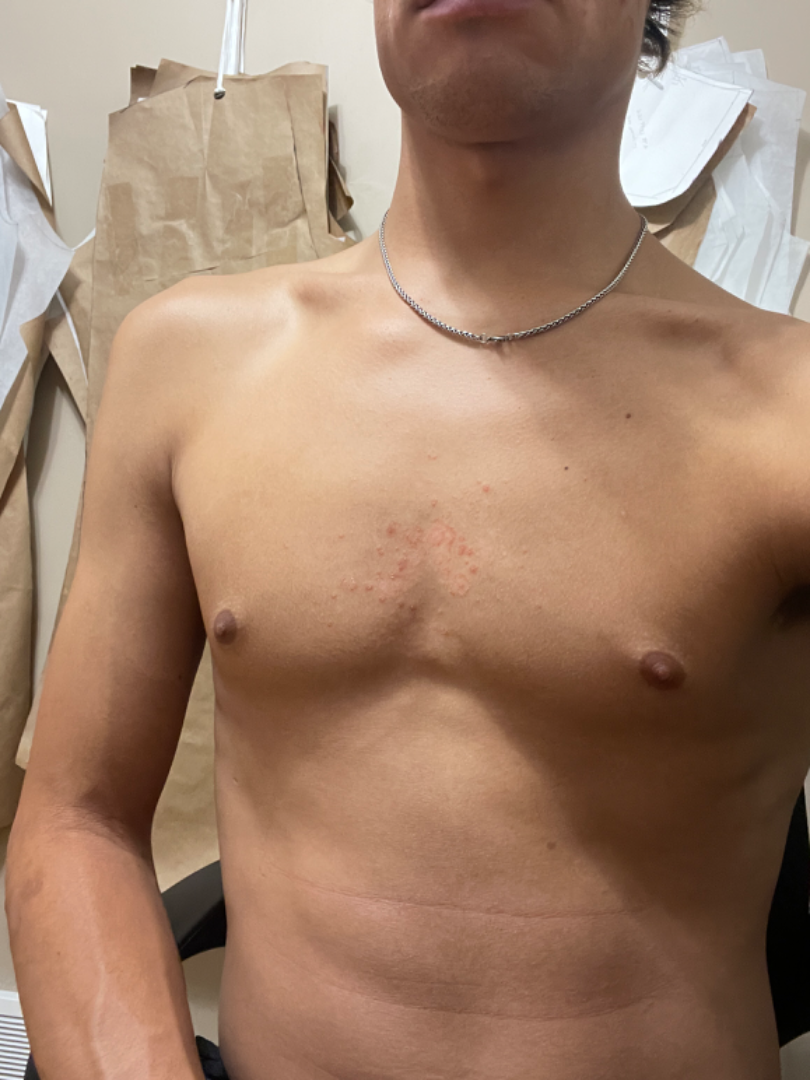– dermatologist impression — Erythema gyratum repens, Seborrheic Dermatitis and Erythema marginatum in acute rheumatic fever were considered with similar weight